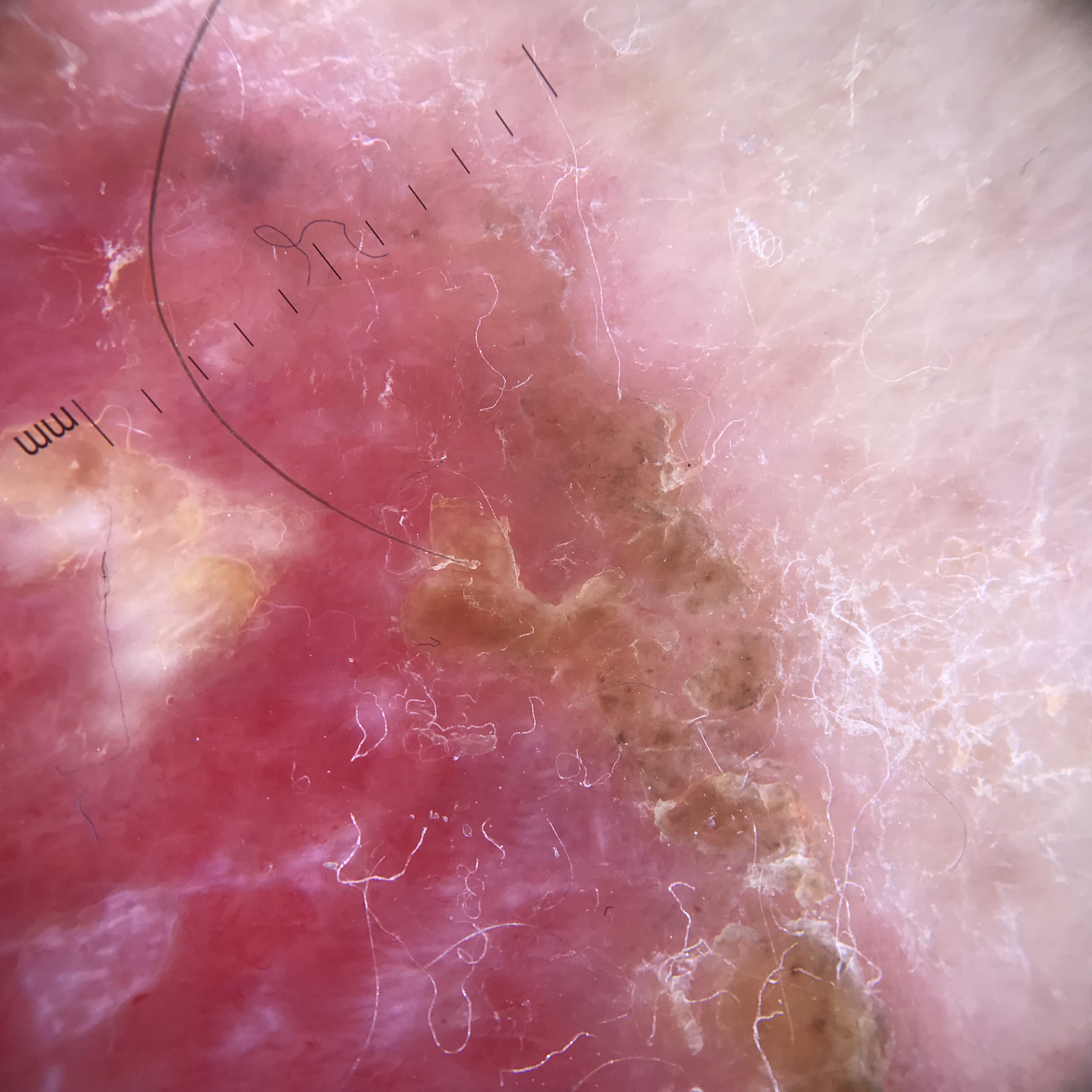Confirmed on histopathology as Bowen's disease.